Acquired for a research image collection, with no referral diagnosis · the patient describes having numerous moles · the patient says their skin reddens with sun exposure:
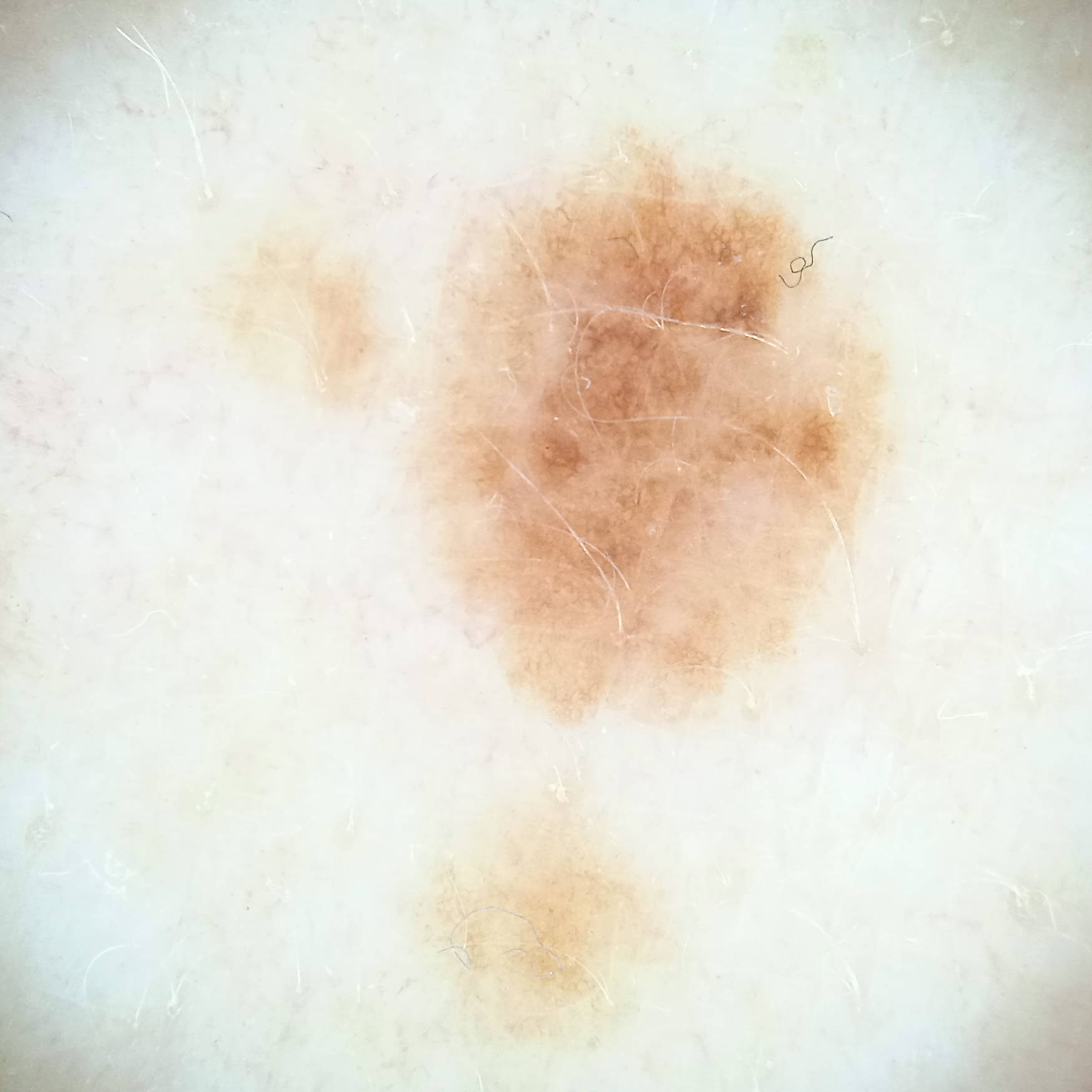diameter: 6.4 mm | diagnostic label: atypical (dysplastic) nevus — dermatologist consensus.